The contributor is 18–29, female; the photograph was taken at a distance; the lesion involves the top or side of the foot, leg, back of the hand and head or neck.
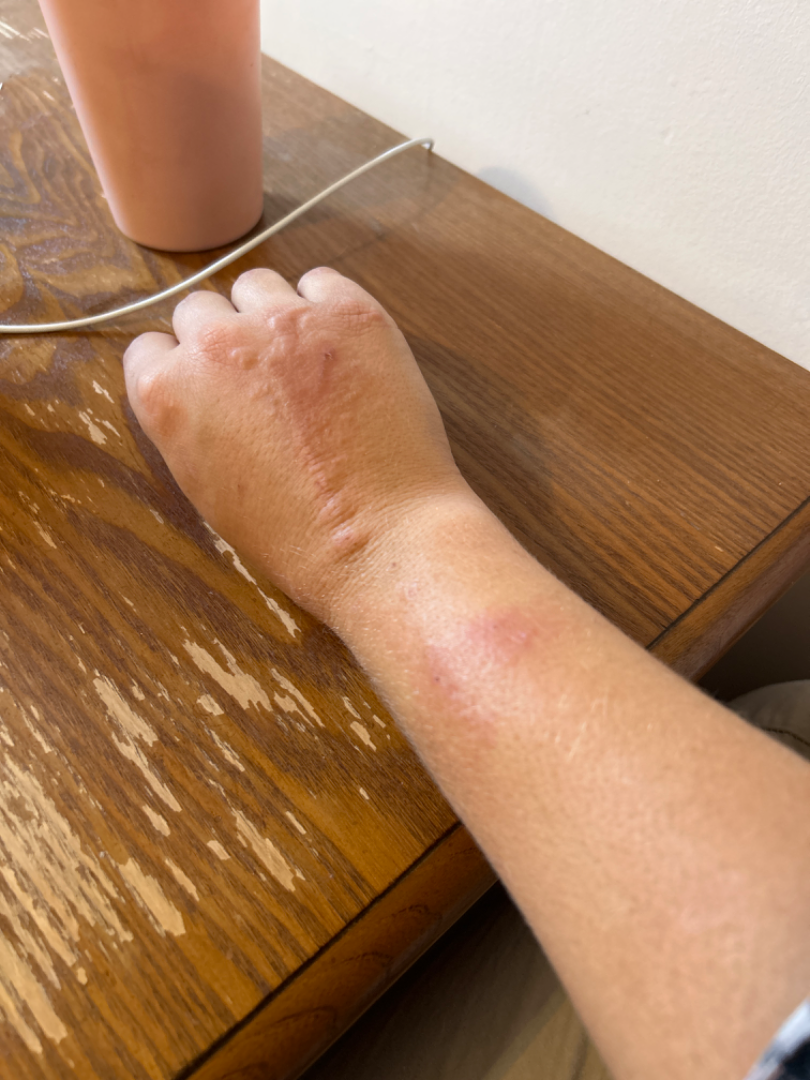| key | value |
|---|---|
| differential | most likely Contact dermatitis; also consider Cat scratch disease; with consideration of Cutaneous sarcoidosis; an alternative is Deep fungal infection |